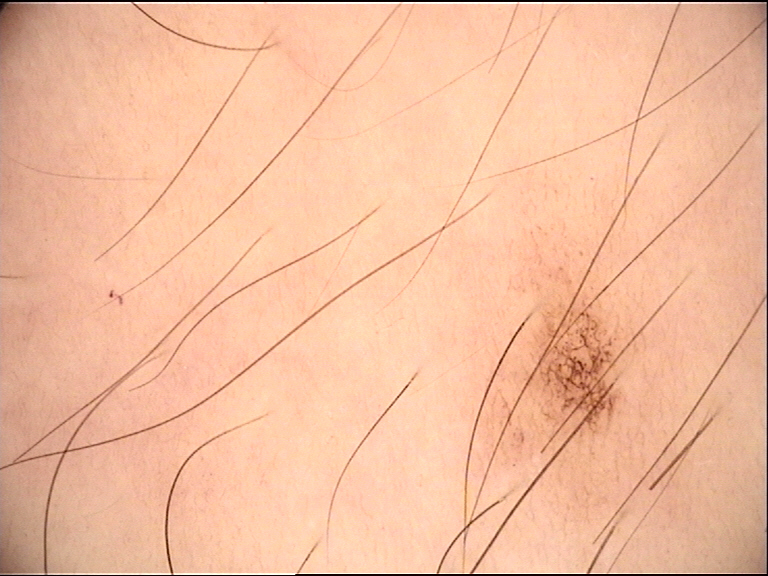{"diagnosis": {"name": "dysplastic junctional nevus", "code": "jd", "malignancy": "benign", "super_class": "melanocytic", "confirmation": "expert consensus"}}